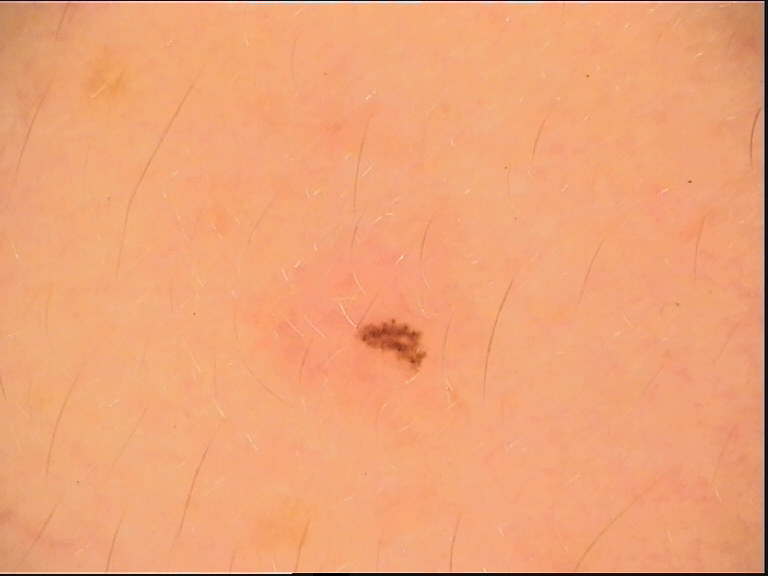Dermoscopy of a skin lesion.
Classified as a dysplastic junctional nevus.